A dermoscopic close-up of a skin lesion.
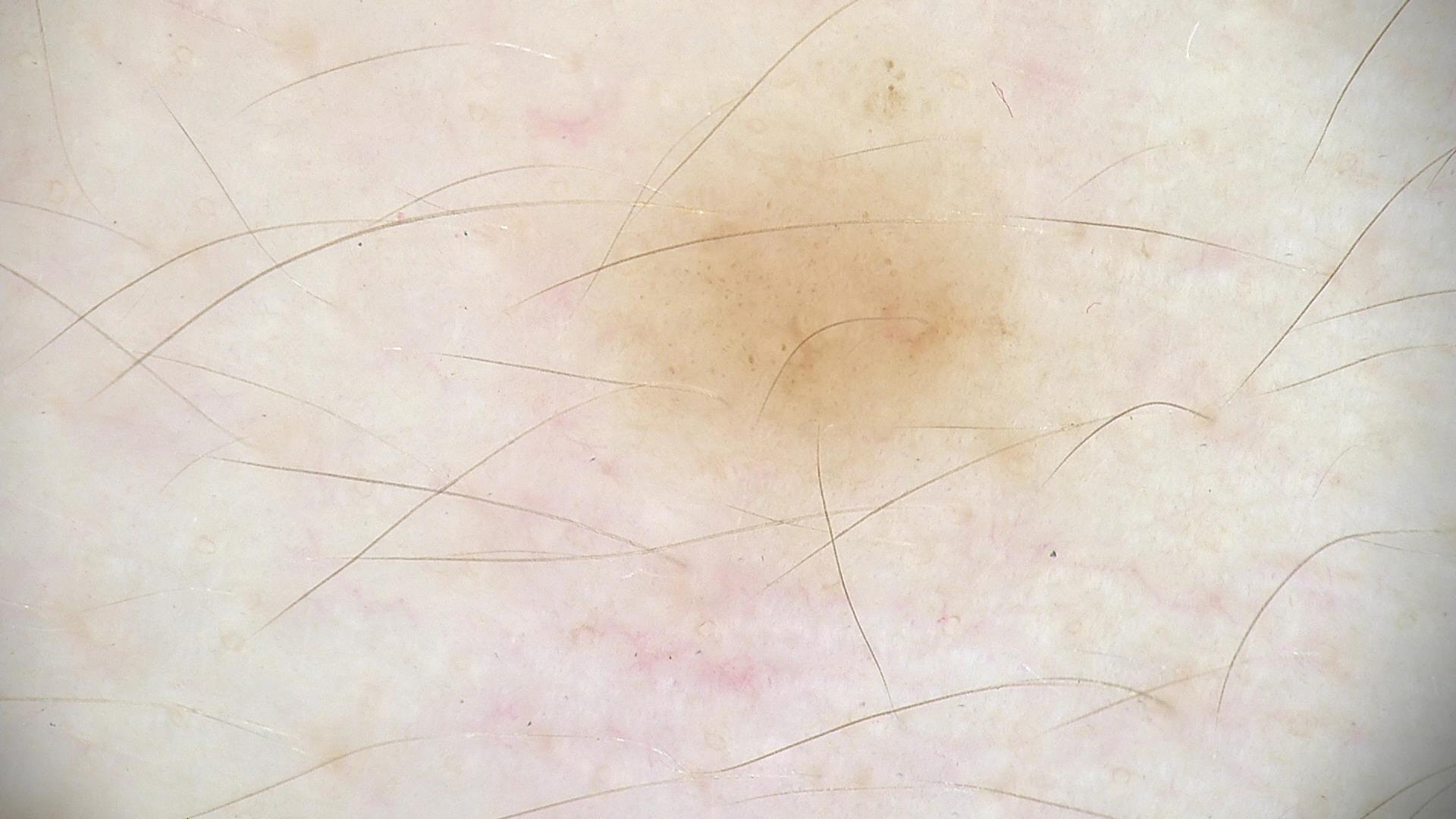Q: What is the diagnosis?
A: dysplastic junctional nevus (expert consensus)